This image was taken at an angle · the affected area is the leg · the contributor is a male aged 30–39:
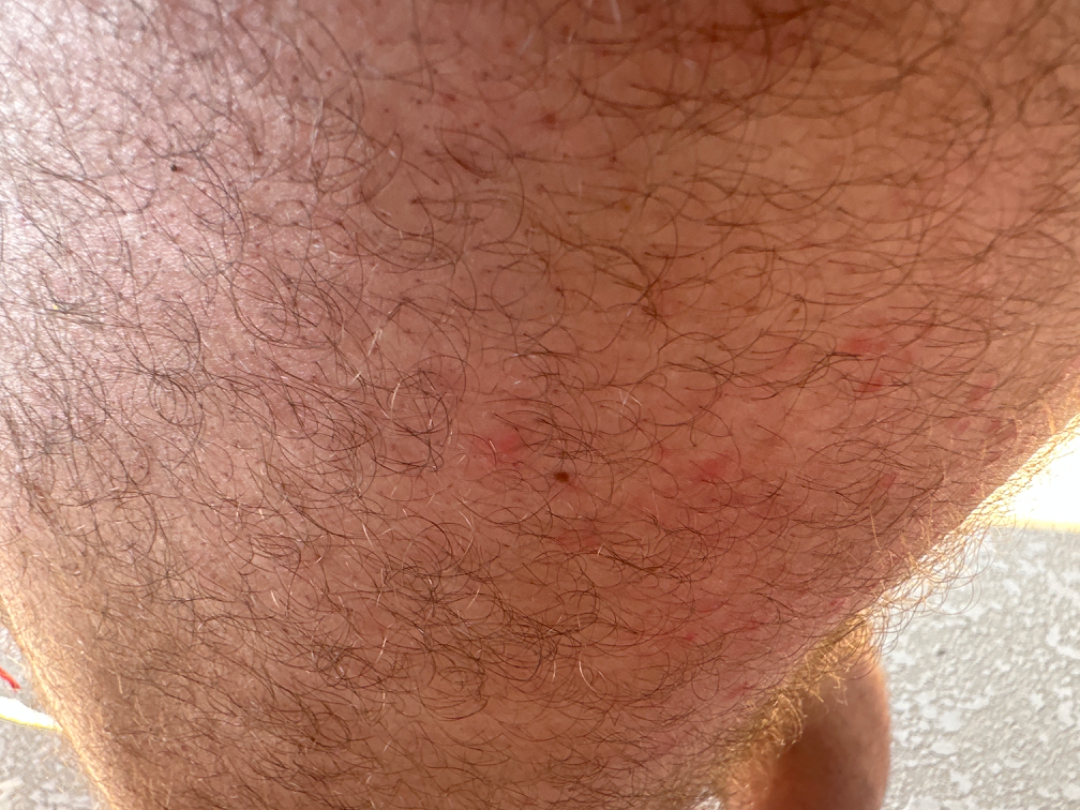Assessment: The skin condition could not be confidently assessed from this image.